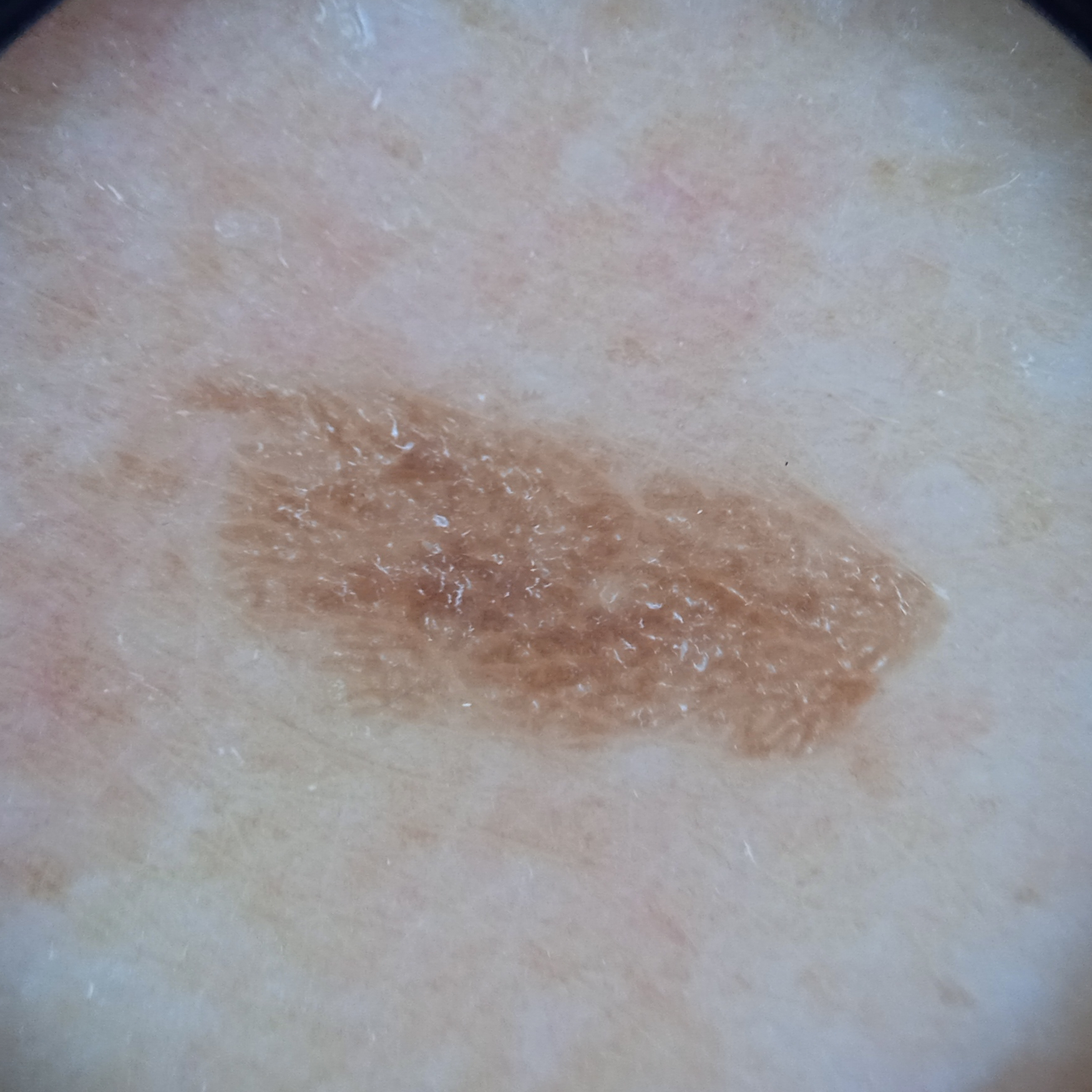A dermoscopy image of a skin lesion.
By self-report, a personal history of cancer and a personal history of skin cancer.
The patient says their skin tans without first burning.
A female subject 75 years of age.
Imaged for a research study, with no referral diagnosis recorded.
The patient describes having a moderate number of moles.
The lesion involves the back.
The lesion measures approximately 8.4 mm.
Four dermatologists reviewed the lesion; the consensus was a seborrheic keratosis; all four reviewers agreed; the reviewers were fairly confident.